Dermoscopy of a skin lesion.
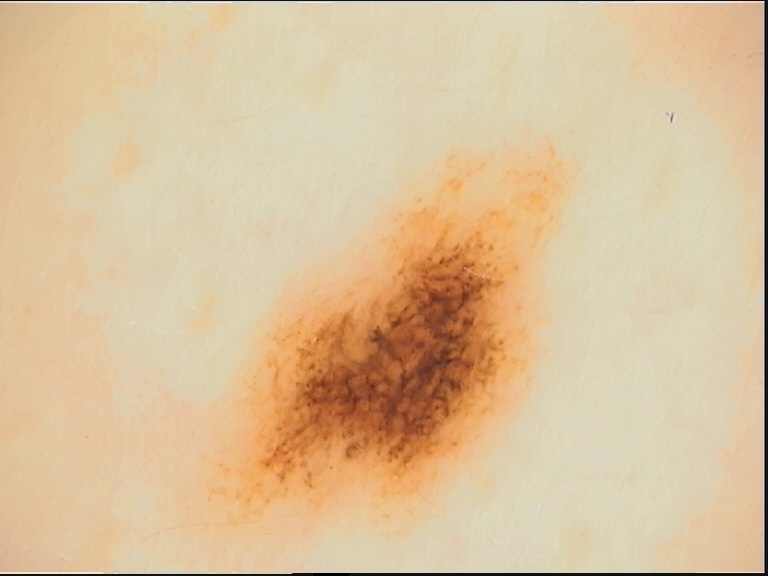Findings:
– diagnostic label — dysplastic junctional nevus (expert consensus)